The patient was assessed as skin type IV; a skin lesion imaged with a dermatoscope; a female subject aged around 55:
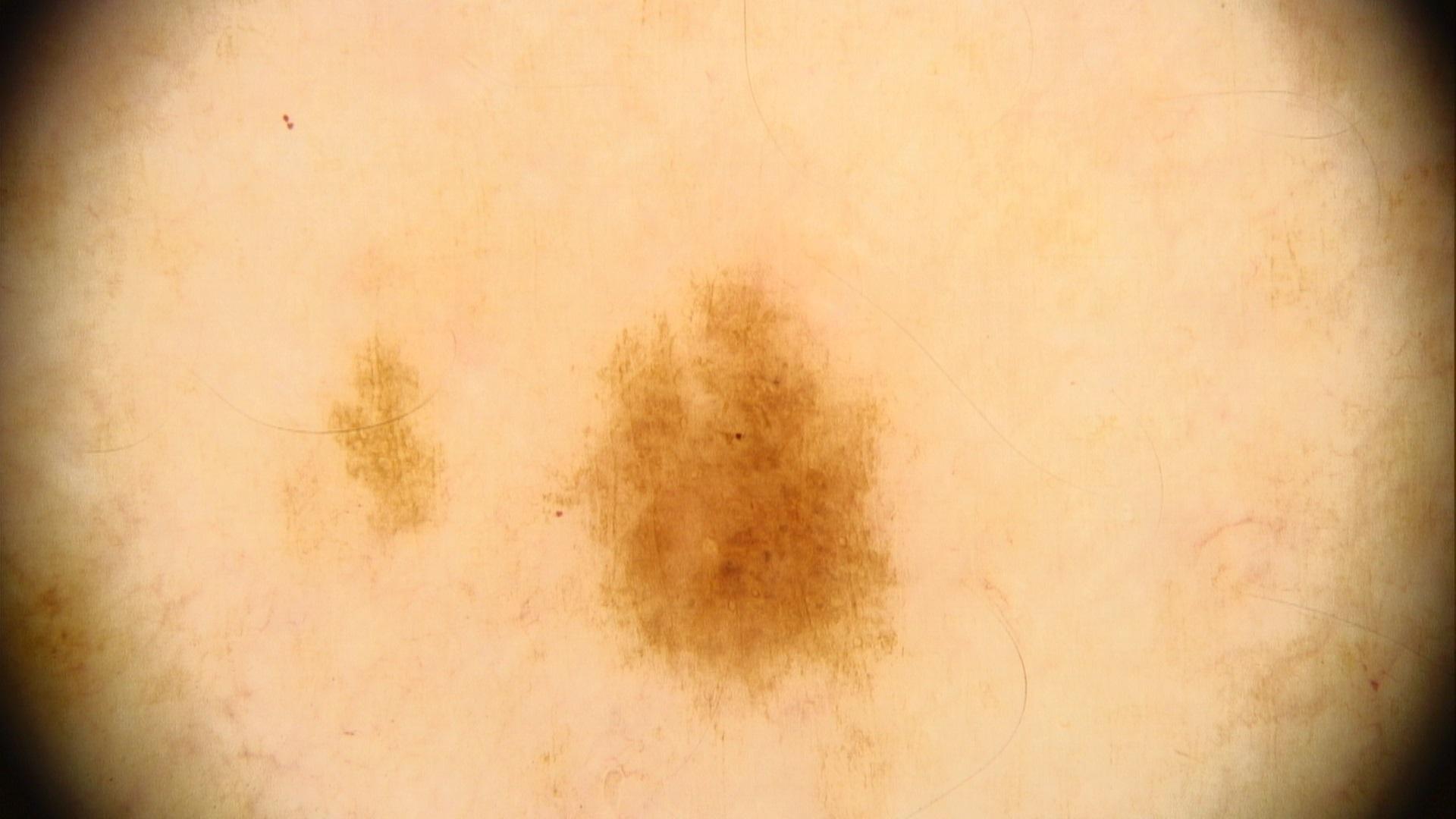anatomic site = the anterior trunk | impression = Nevus.